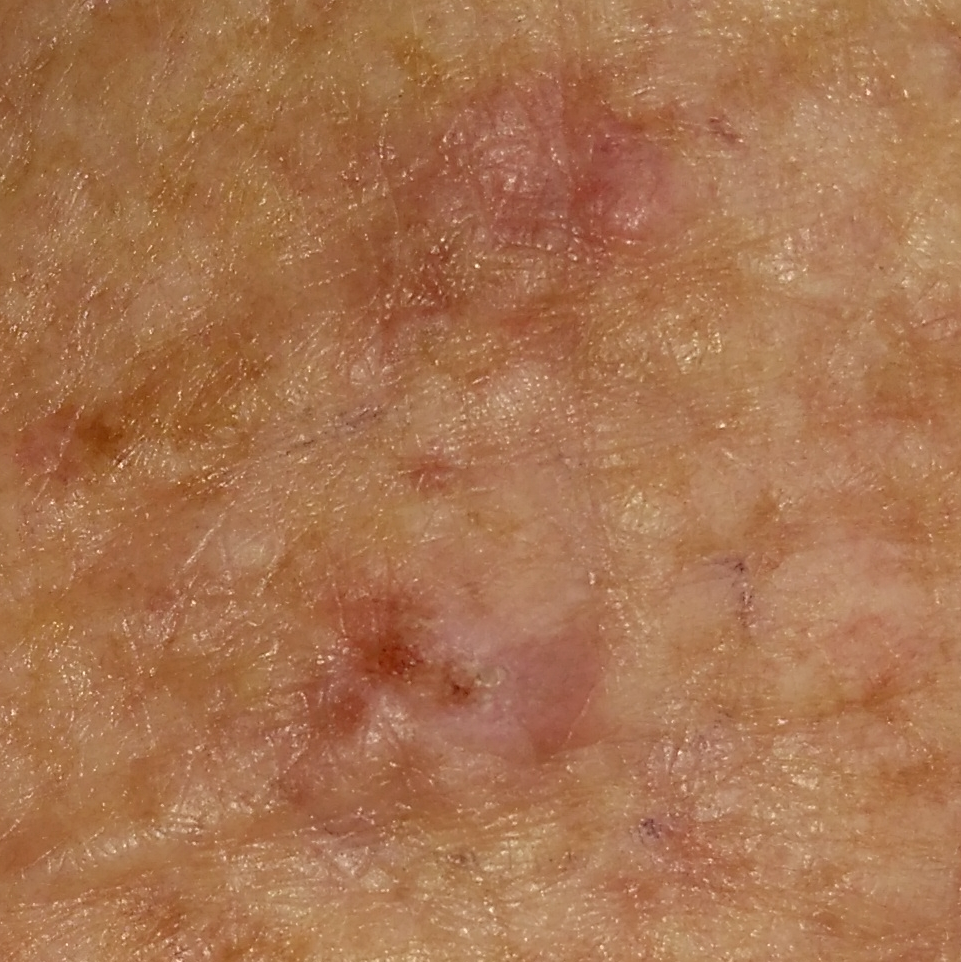risk factors — prior malignancy (patient or family); imaging — clinical photograph; FST — II; body site — an arm; lesion diameter — 8x7 mm; patient-reported symptoms — elevation; pathology — squamous cell carcinoma (biopsy-proven).